A dermoscopy image of a single skin lesion.
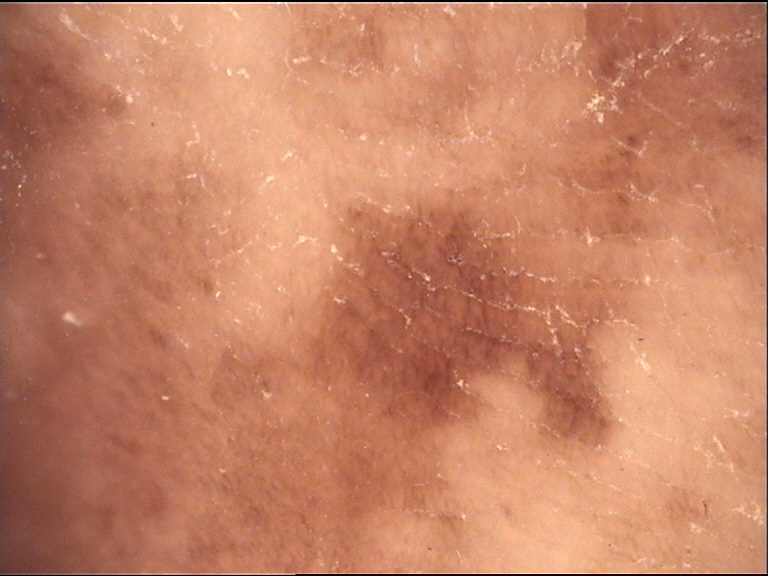label — acral lentiginous melanoma (biopsy-proven)